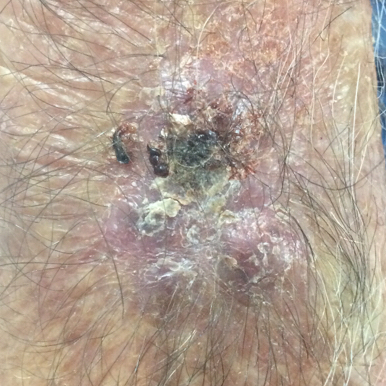image=smartphone clinical photo | skin phototype=III | exposures=prior malignancy (patient or family), tobacco use, pesticide exposure, alcohol use | body site=a forearm | lesion size=26x20 mm | reported symptoms=bleeding, itching, elevation | pathology=squamous cell carcinoma (biopsy-proven).